A subject age 77; a clinical close-up photograph of a skin lesion: 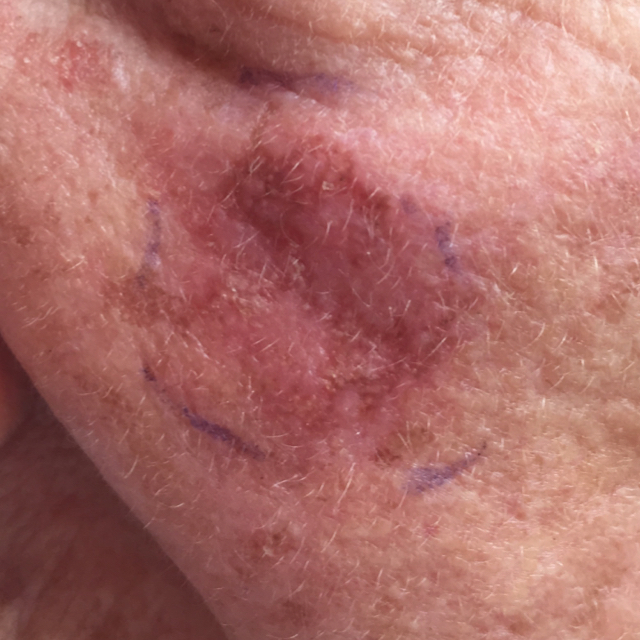body site = the face | symptoms = itching | diagnostic label = actinic keratosis (clinical consensus).